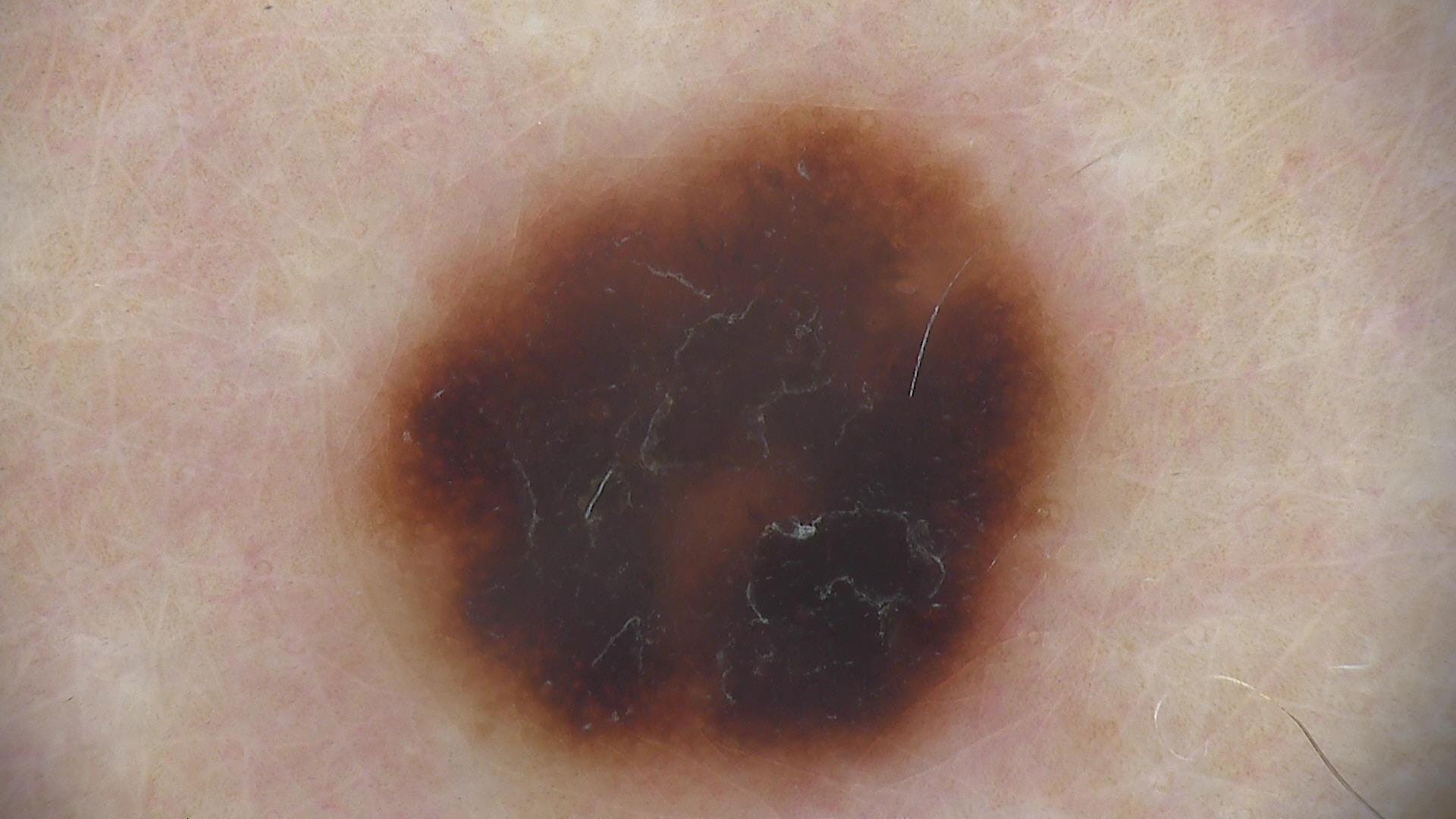Summary:
A dermoscopy image of a single skin lesion.
Impression:
The diagnostic label was a benign lesion — a dysplastic compound nevus.